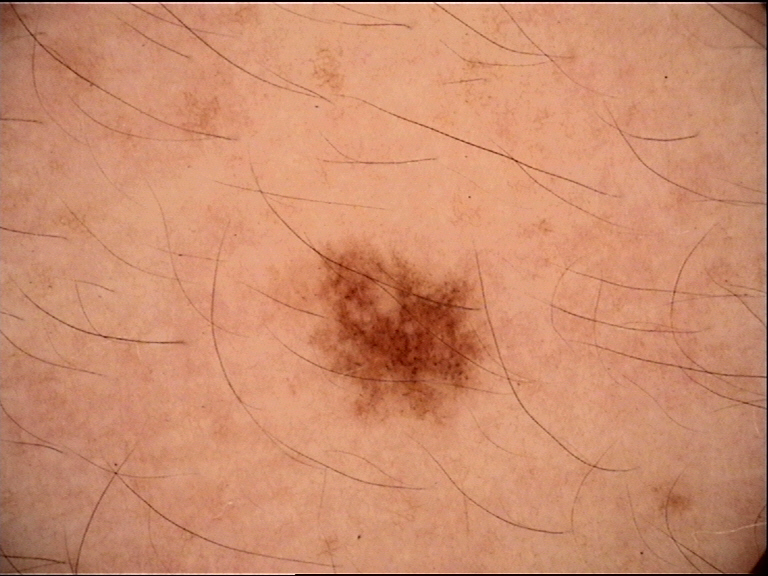Classified as a junctional nevus.